Close-up view.
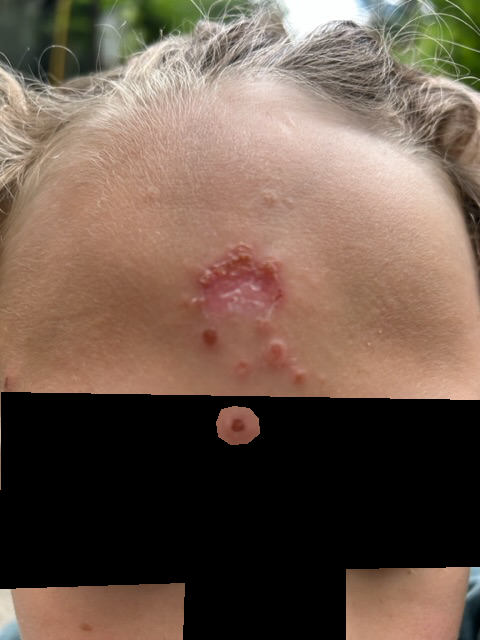symptoms: itching and enlargement
self-categorized as: a rash
texture: raised or bumpy
present for: one to four weeks
impression: the differential is split between Impetigo and Tinea